The affected area is the back of the torso and arm · female subject, age 40–49 · this image was taken at a distance.
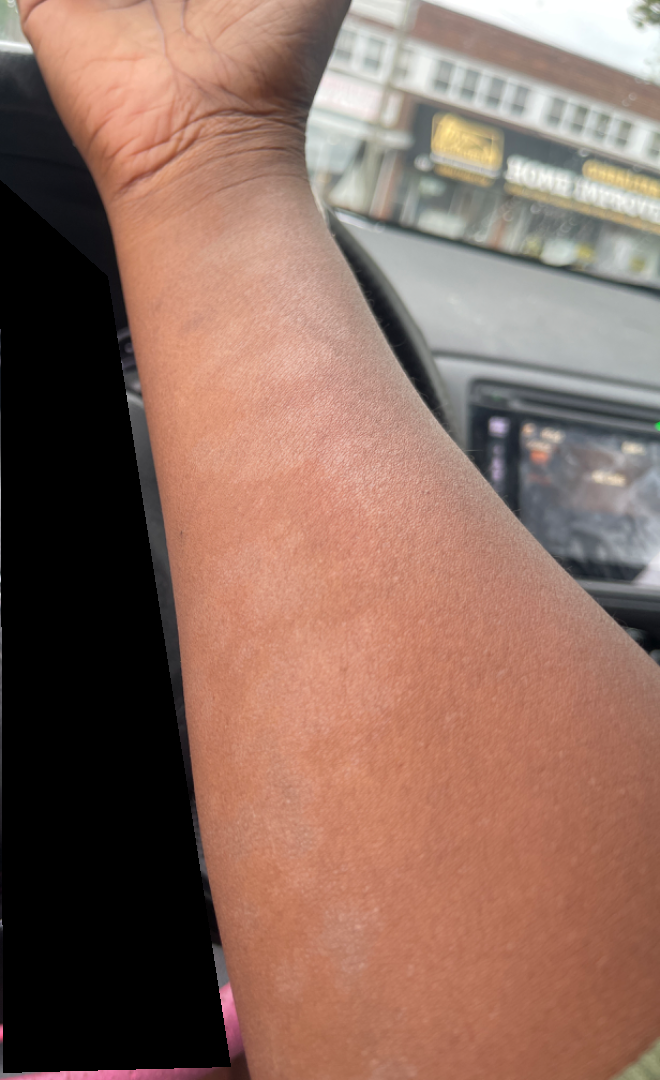The patient notes the condition has been present for three to twelve months.
The lesion is associated with itching.
The patient considered this a rash.
On remote review of the image, Pityriasis alba (considered); Vitiligo (considered); Post-Inflammatory hypopigmentation (considered).